The photograph was taken at an angle; located on the leg; the patient reported no systemic symptoms; the lesion is described as raised or bumpy; male patient, age 18–29; the patient described the issue as a rash; symptoms reported: itching — 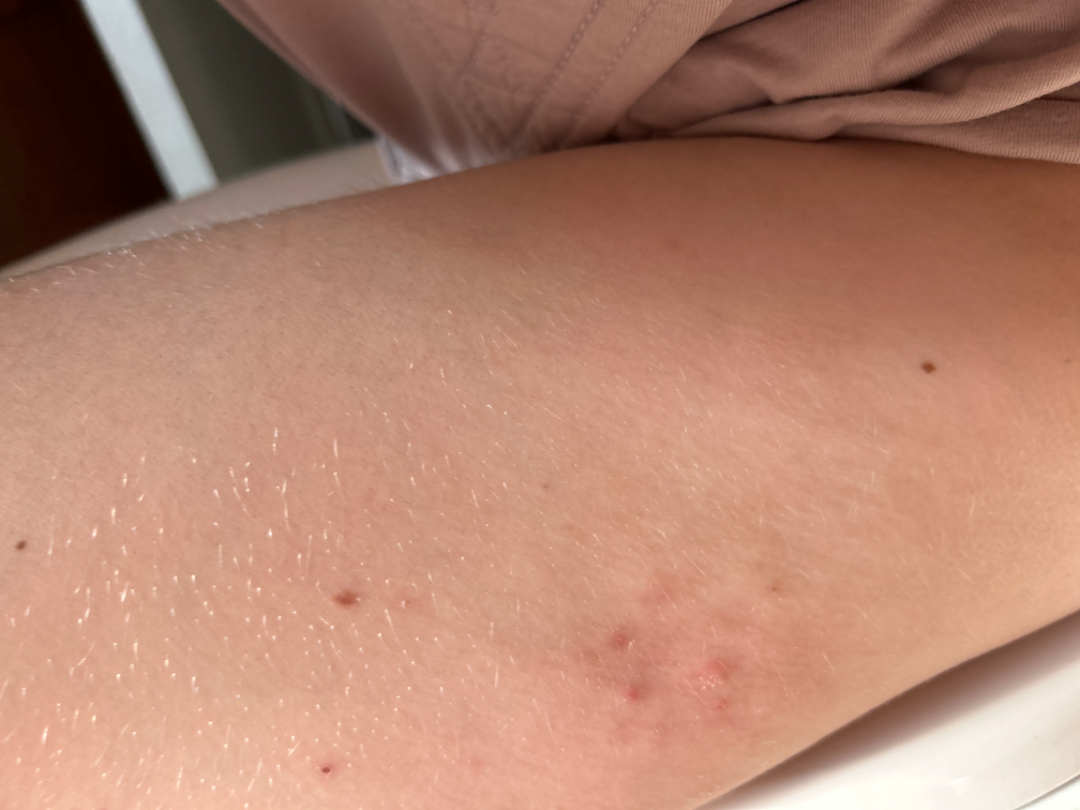Assessment: The skin condition could not be confidently assessed from this image.